A dermoscopy image of a single skin lesion, the subject is a female in their 60s:
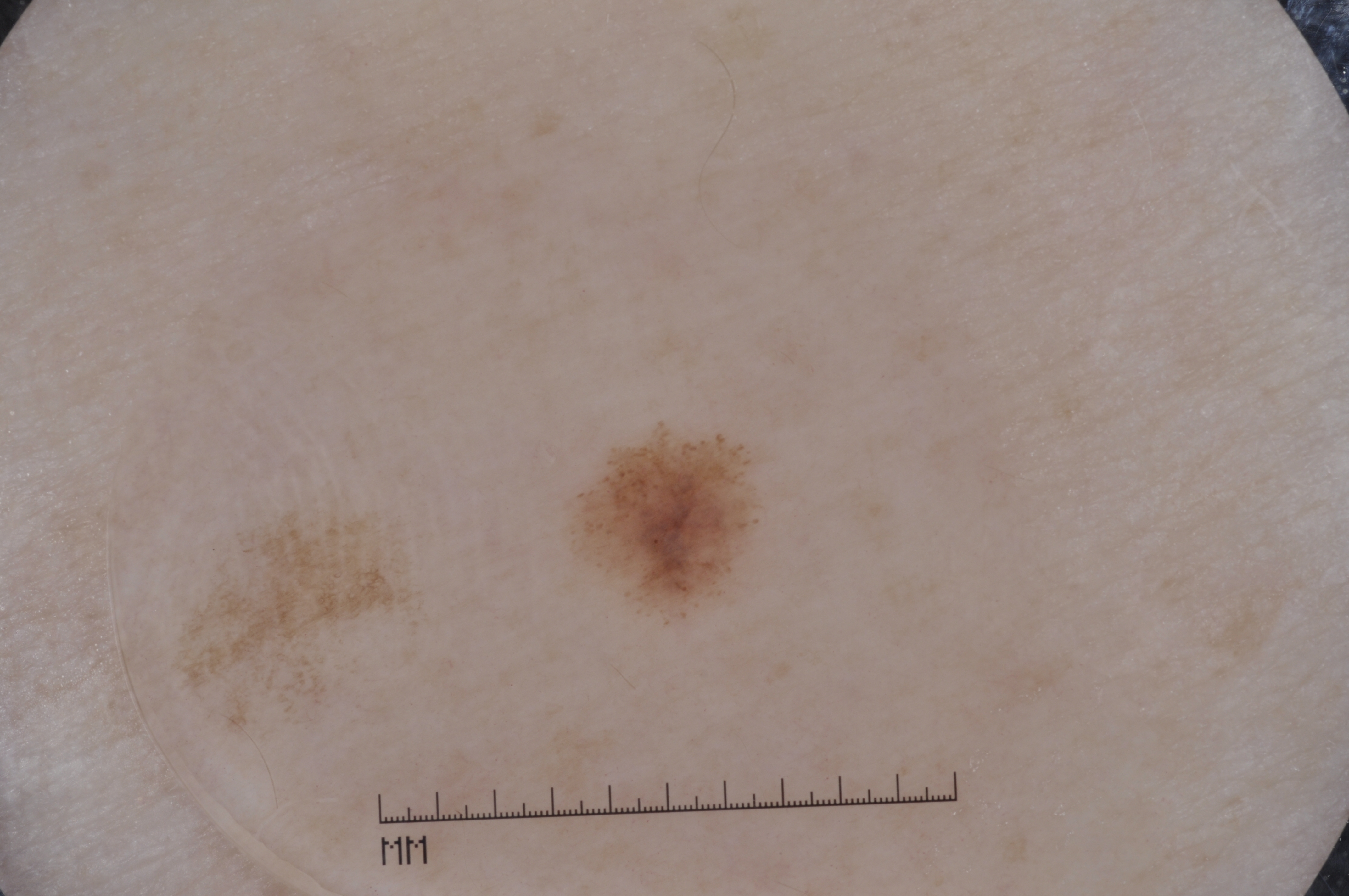lesion location = 565 421 763 625 | absent dermoscopic findings = streaks, negative network, pigment network, and milia-like cysts | diagnostic label = a melanocytic nevus, a benign skin lesion.